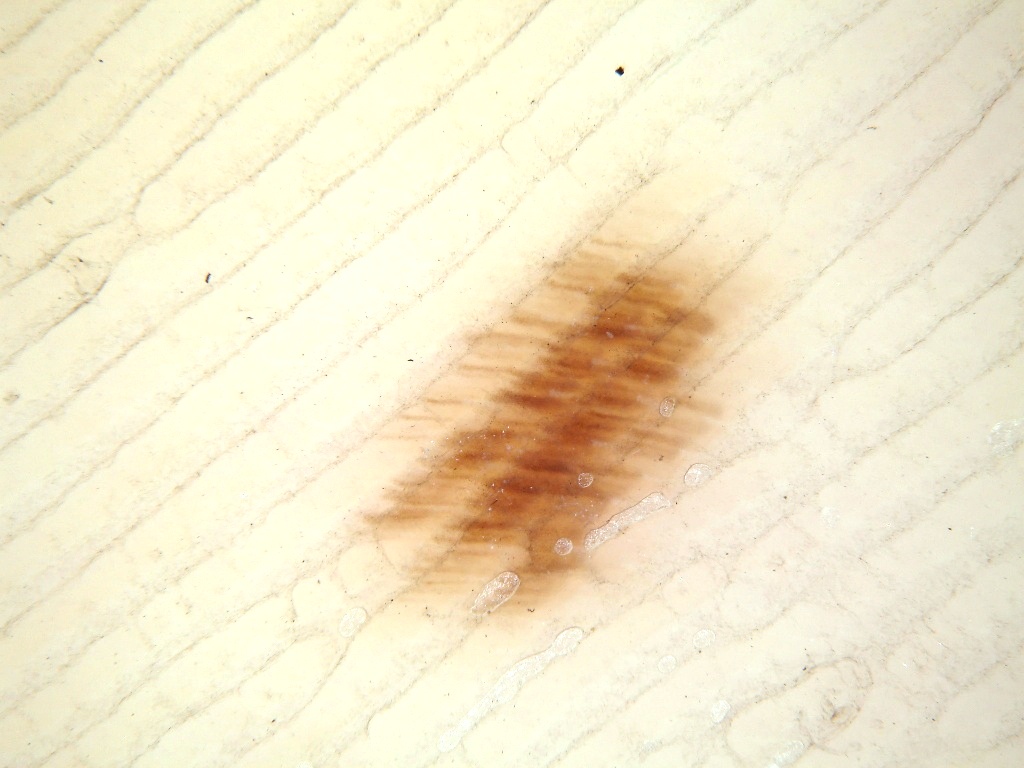patient = female, aged approximately 20
modality = dermatoscopic image of a skin lesion
dermoscopic features assessed but absent = streaks, negative network, globules, milia-like cysts, and pigment network
lesion bbox = left=344, top=162, right=798, bottom=639
assessment = a melanocytic nevus, a benign skin lesion